This image was taken at an angle.
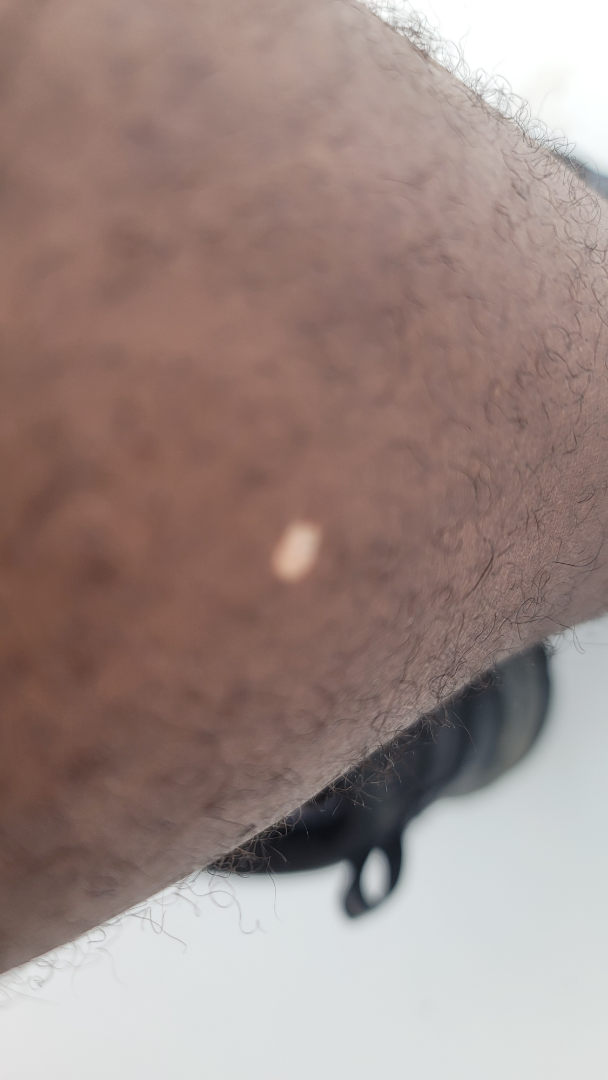Impression: The reviewer was unable to grade this case for skin condition.